No relevant systemic symptoms · Fitzpatrick skin type IV; non-clinician graders estimated MST 3 or 4 · male contributor, age 50–59 · this is a close-up image · located on the leg · the patient described the issue as a rash · the contributor notes the lesion is raised or bumpy · the contributor notes itching: 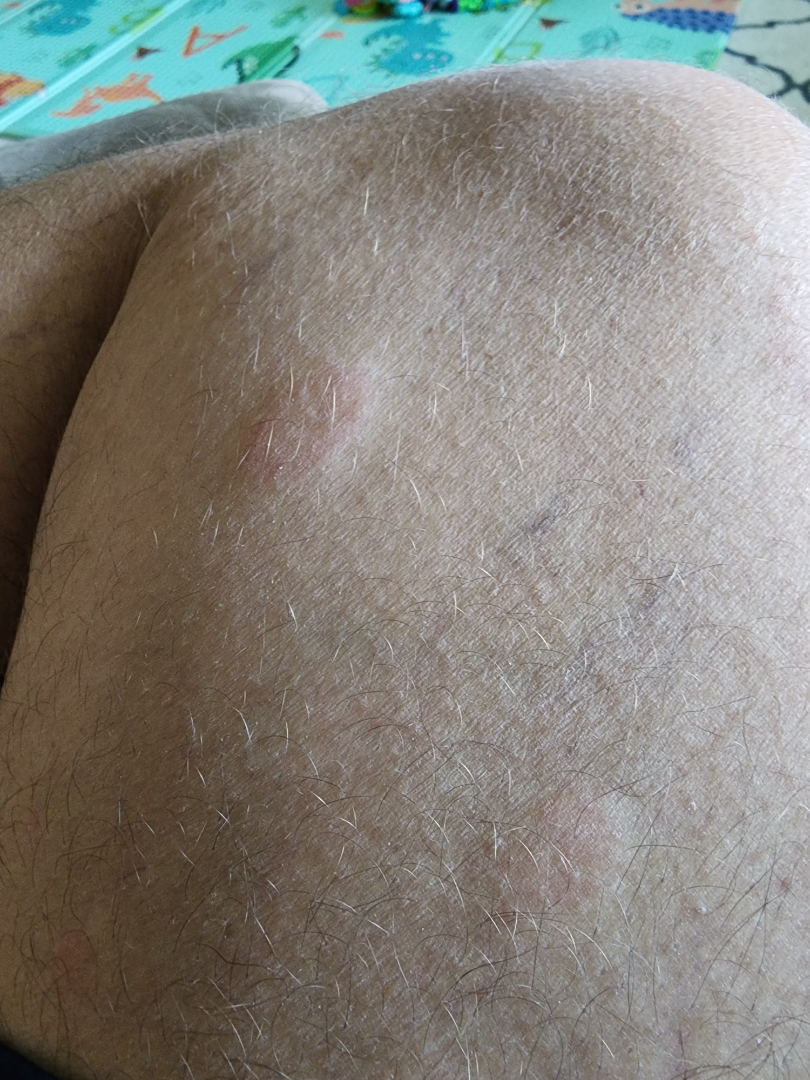assessment — indeterminate from the photograph.